The affected area is the arm, the photograph was taken at a distance:
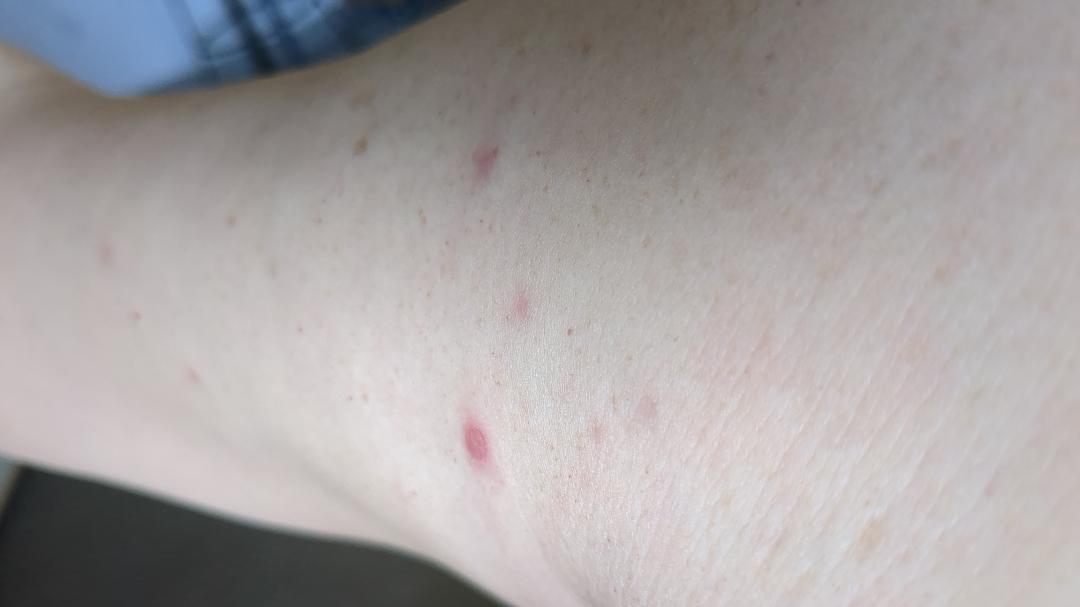Findings:
* assessment: could not be assessed
* skin tone: non-clinician graders estimated MST 1 (US pool) or 2 (India pool)
* surface texture: raised or bumpy
* other reported symptoms: none reported
* self-categorized as: a rash
* lesion symptoms: bothersome appearance